No associated systemic symptoms reported; present for less than one week; located on the leg and top or side of the foot; this is a close-up image; no relevant lesion symptoms reported; the lesion is described as rough or flaky; the patient described the issue as a rash.
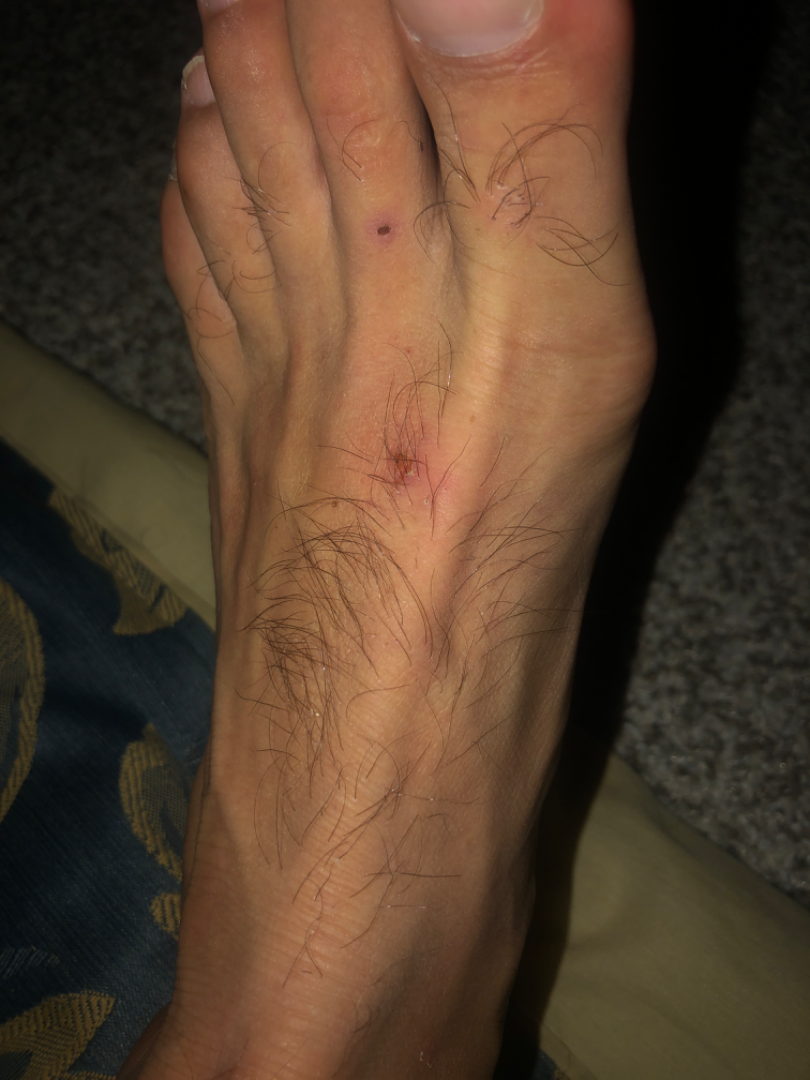Findings: On teledermatology review, the impression was split between Abrasion, scrape, or scab; Inflicted skin lesions; and Insect Bite.